A dermatoscopic image of a skin lesion · a male patient, about 40 years old:
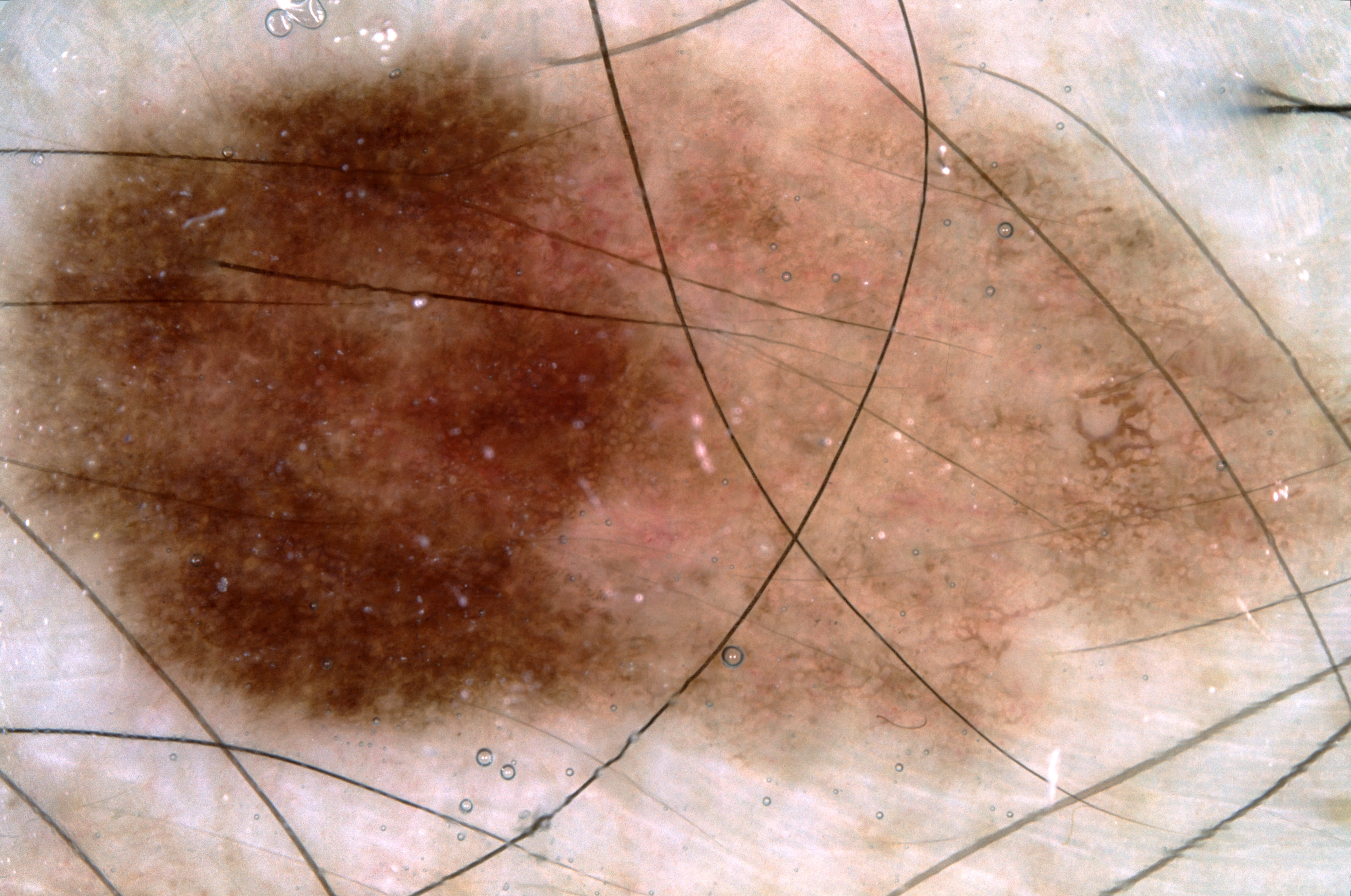With coordinates (x1, y1, x2, y2), the lesion's extent is <bbox>4, 2, 1345, 794</bbox>. On dermoscopy, the lesion shows negative network, pigment network, and milia-like cysts. The clinical diagnosis was a melanocytic nevus.